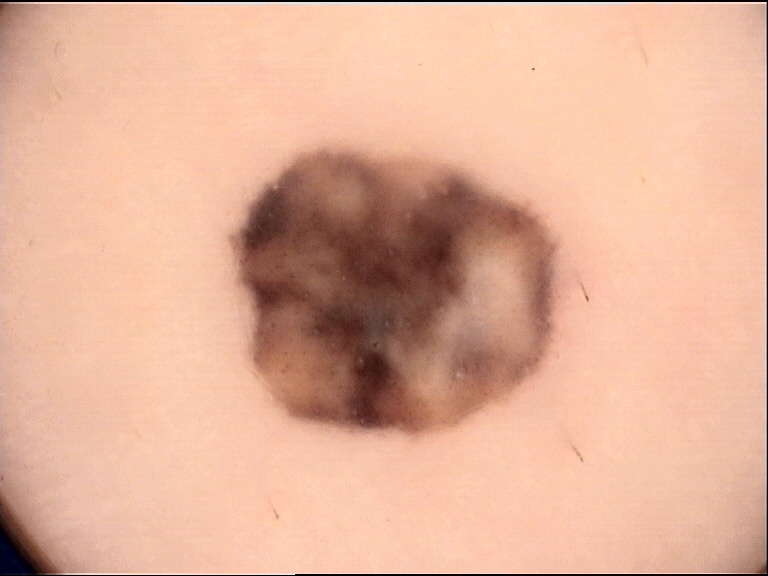Dermoscopy of a skin lesion.
This is a dermal, banal lesion.
The diagnostic label was a blue nevus.